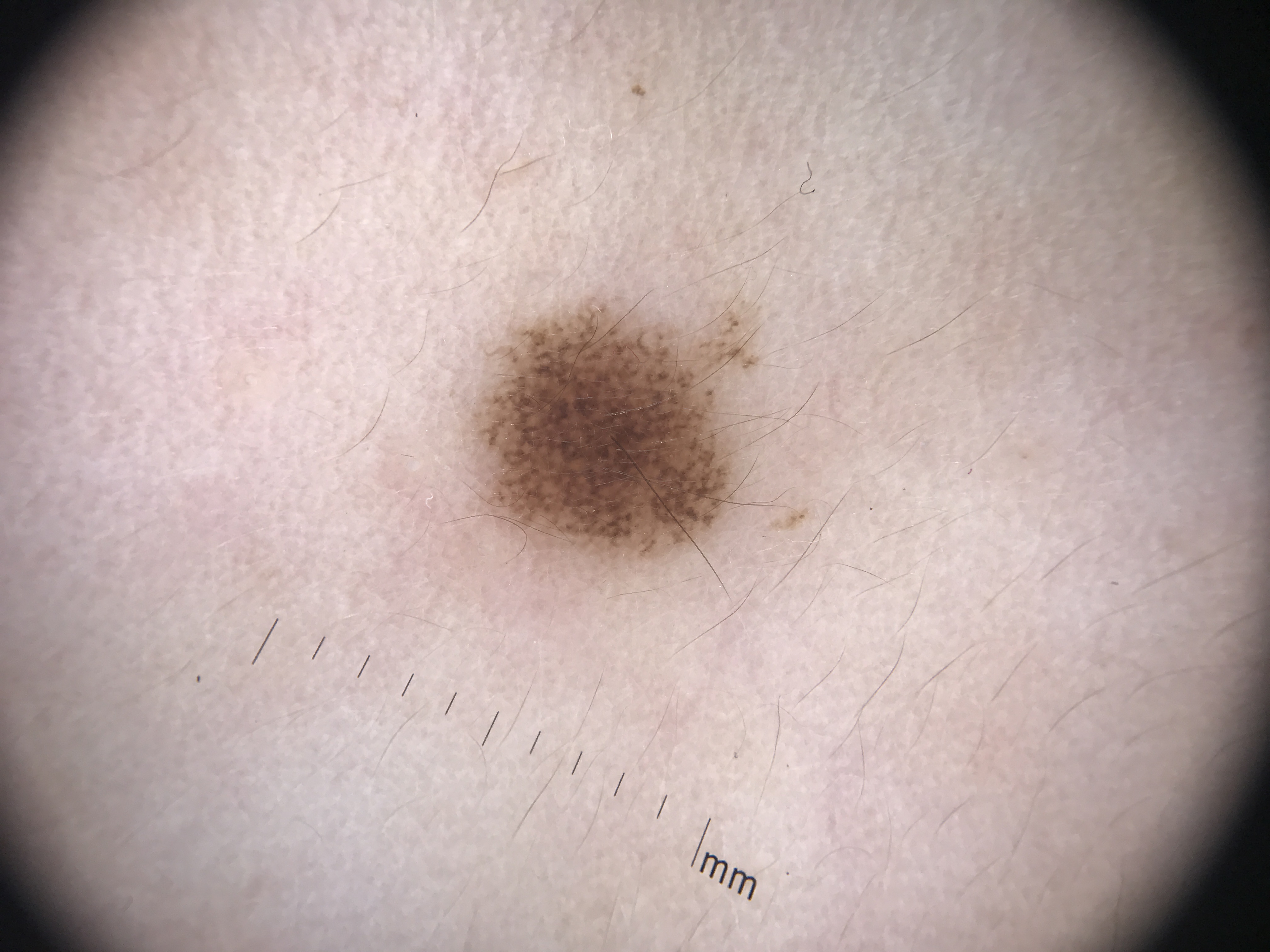A dermoscopic close-up of a skin lesion.
Labeled as a benign lesion — a dysplastic junctional nevus.